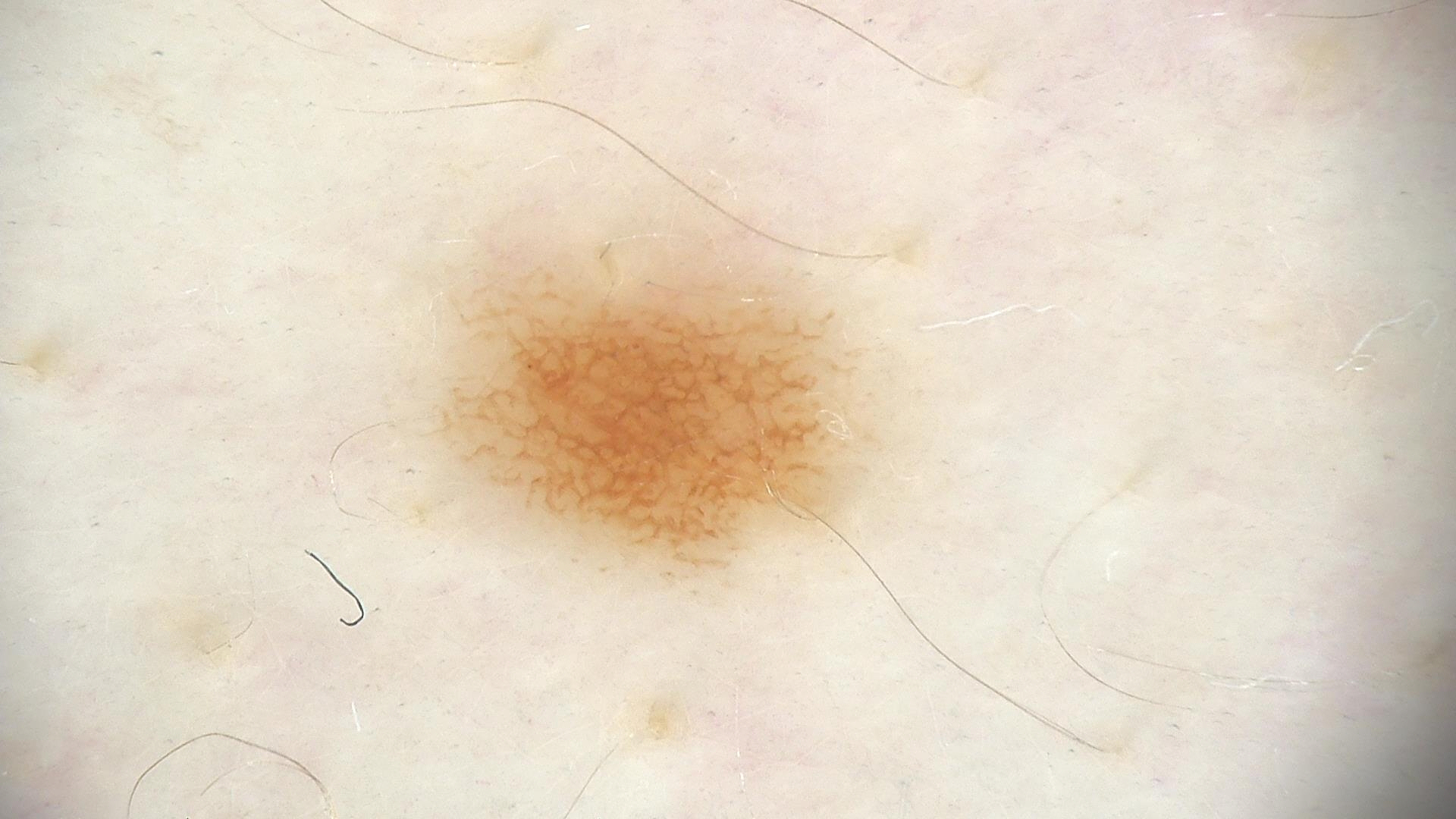Findings:
A dermoscopic photograph of a skin lesion. The morphology is that of a banal lesion.
Conclusion:
Labeled as a junctional nevus.